By history, pesticide exposure, tobacco use, no prior malignancy (patient or family), and no alcohol use; a smartphone photograph of a skin lesion; recorded as Fitzpatrick I; a male subject aged 54 — 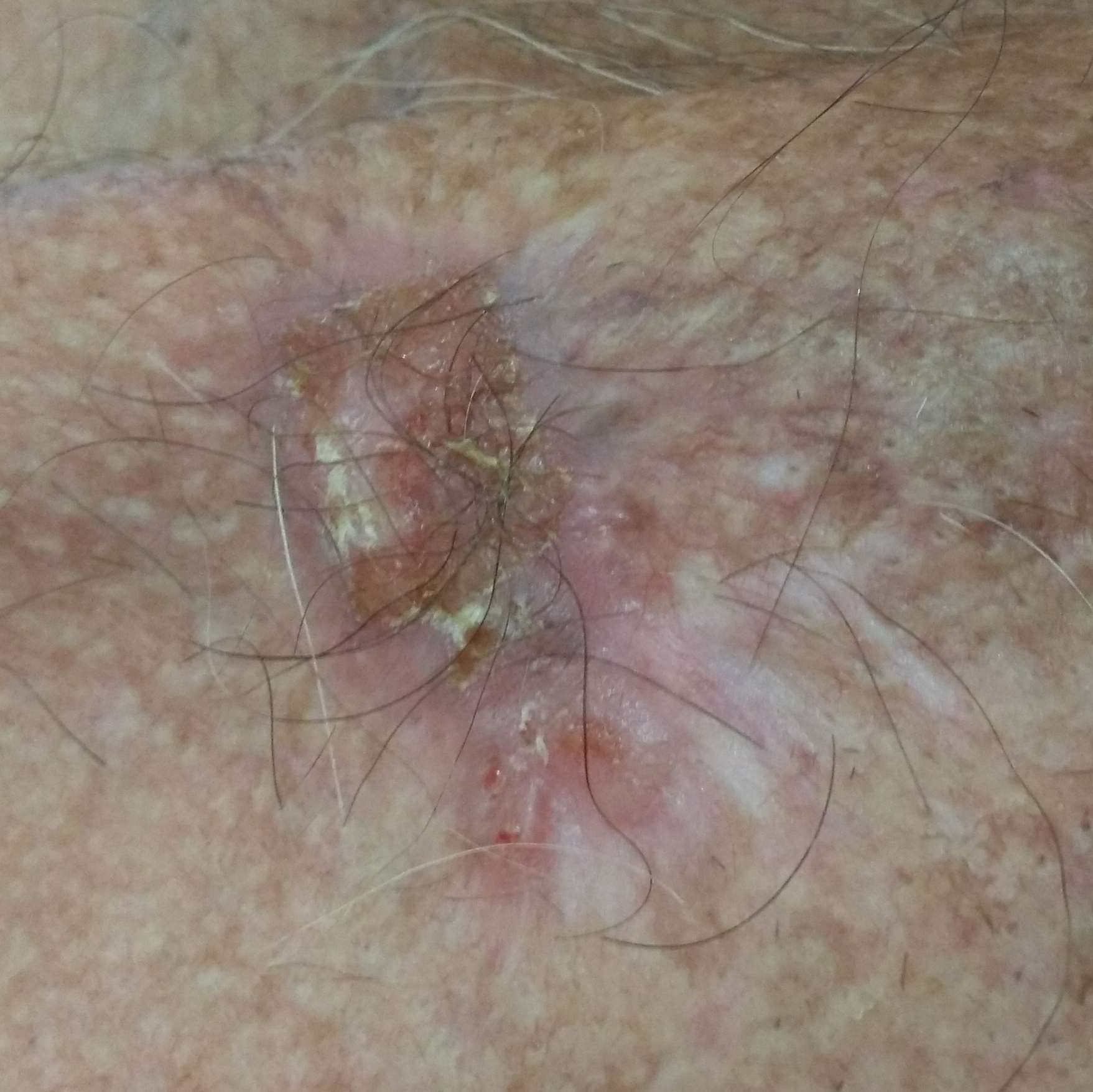The lesion is on the chest. The lesion measures 35 × 20 mm. Per patient report, the lesion has bled, is elevated, itches, hurts, and has grown. Histopathological examination showed a skin cancer — a basal cell carcinoma.